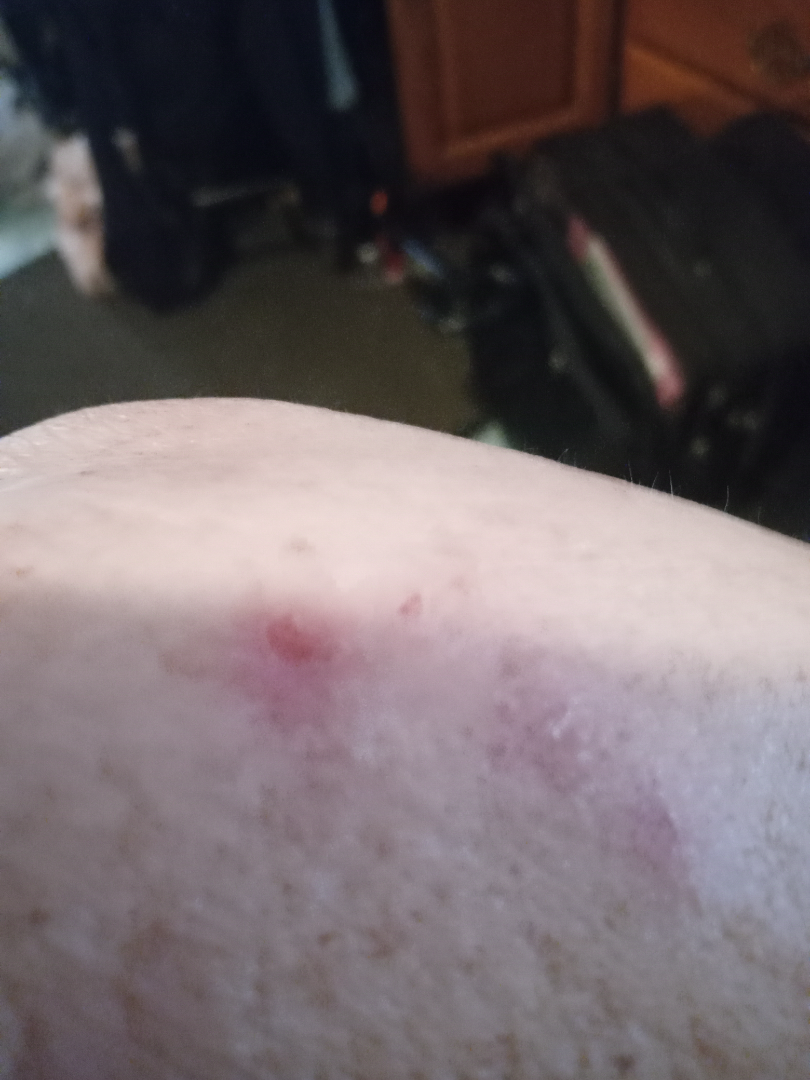The reviewing dermatologist was unable to assign a differential diagnosis from the image. The photograph is a close-up of the affected area. The condition has been present for one to four weeks. The patient described the issue as a rash. The affected area is the arm.